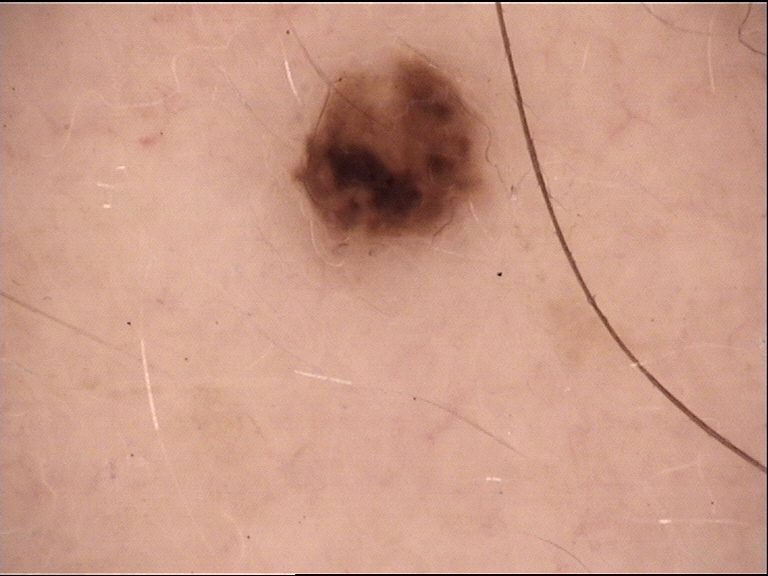| field | value |
|---|---|
| assessment | compound nevus (expert consensus) |